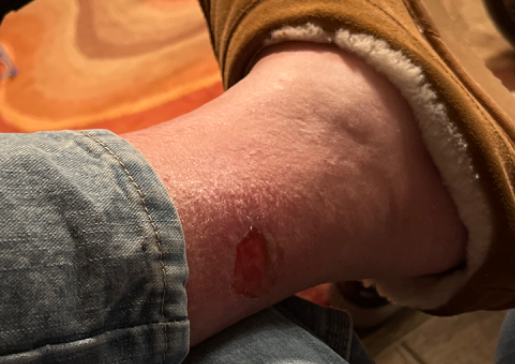The photo was captured at a distance. The contributor reports the condition has been present for less than one week. Texture is reported as fluid-filled and rough or flaky. The affected area is the leg. On remote dermatologist review: Erosion of skin (considered); Abrasion, scrape, or scab (considered); Traumatic blister (considered).